A close-up photograph; located on the leg and front of the torso; the lesion is described as raised or bumpy; no relevant systemic symptoms; reported duration is one to four weeks; the contributor reports itching; the patient is a female aged 18–29; the patient considered this a rash.
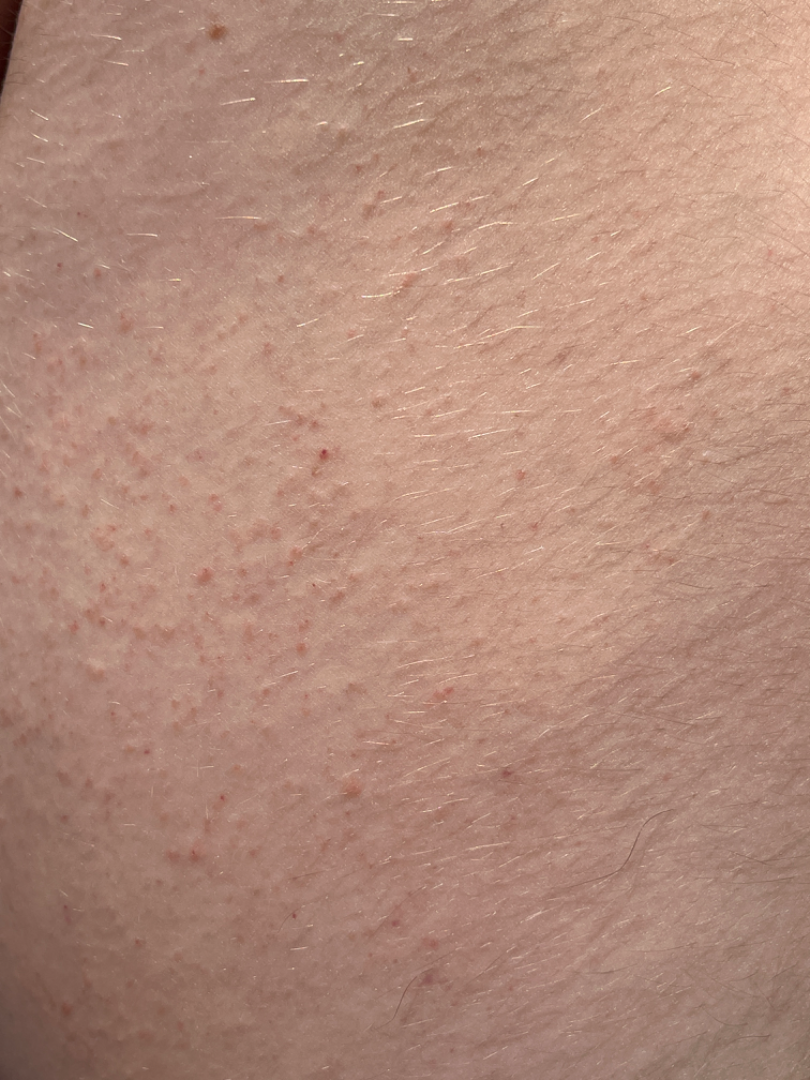assessment = Keratosis pilaris (favored); Miliaria (unlikely); Folliculitis (unlikely); Eczema (unlikely).